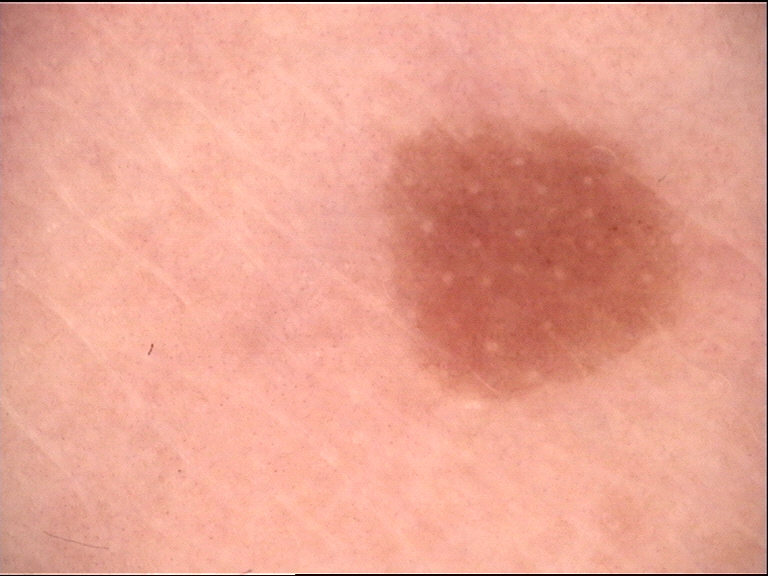Case:
- modality: dermoscopy
- diagnosis: acral dysplastic junctional nevus (expert consensus)